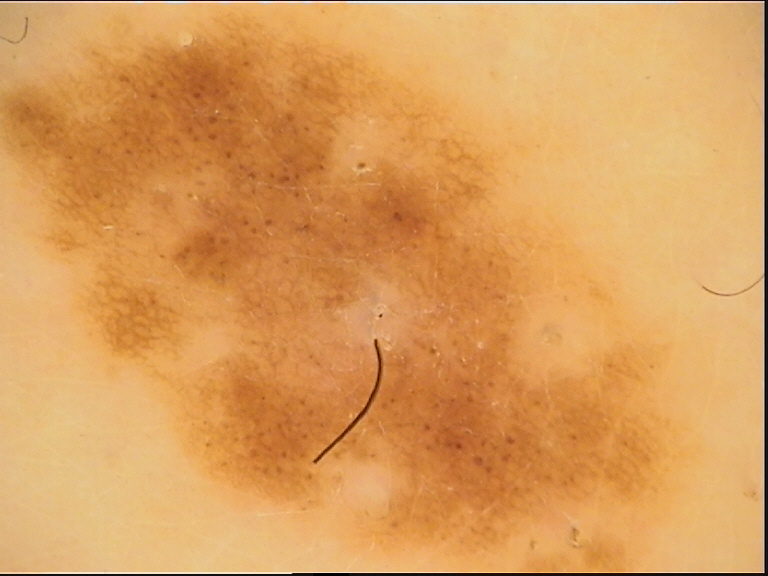Findings:
• image type: dermoscopy
• diagnostic label: dysplastic compound nevus (expert consensus)